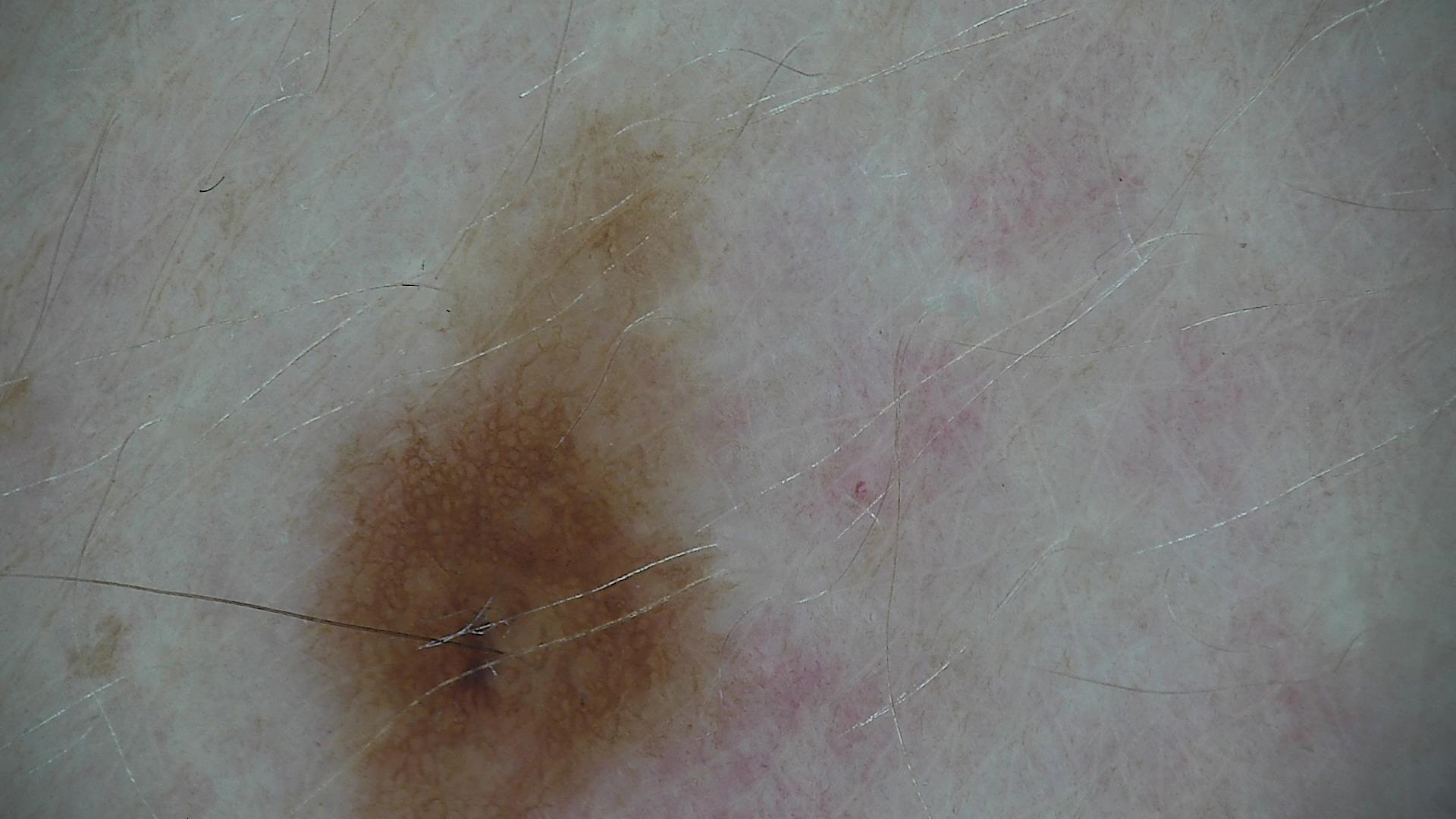  image: dermoscopy
  diagnosis:
    name: compound nevus
    code: cb
    malignancy: benign
    super_class: melanocytic
    confirmation: expert consensus